The subject is a male aged 33 to 37. Dermoscopy of a skin lesion.
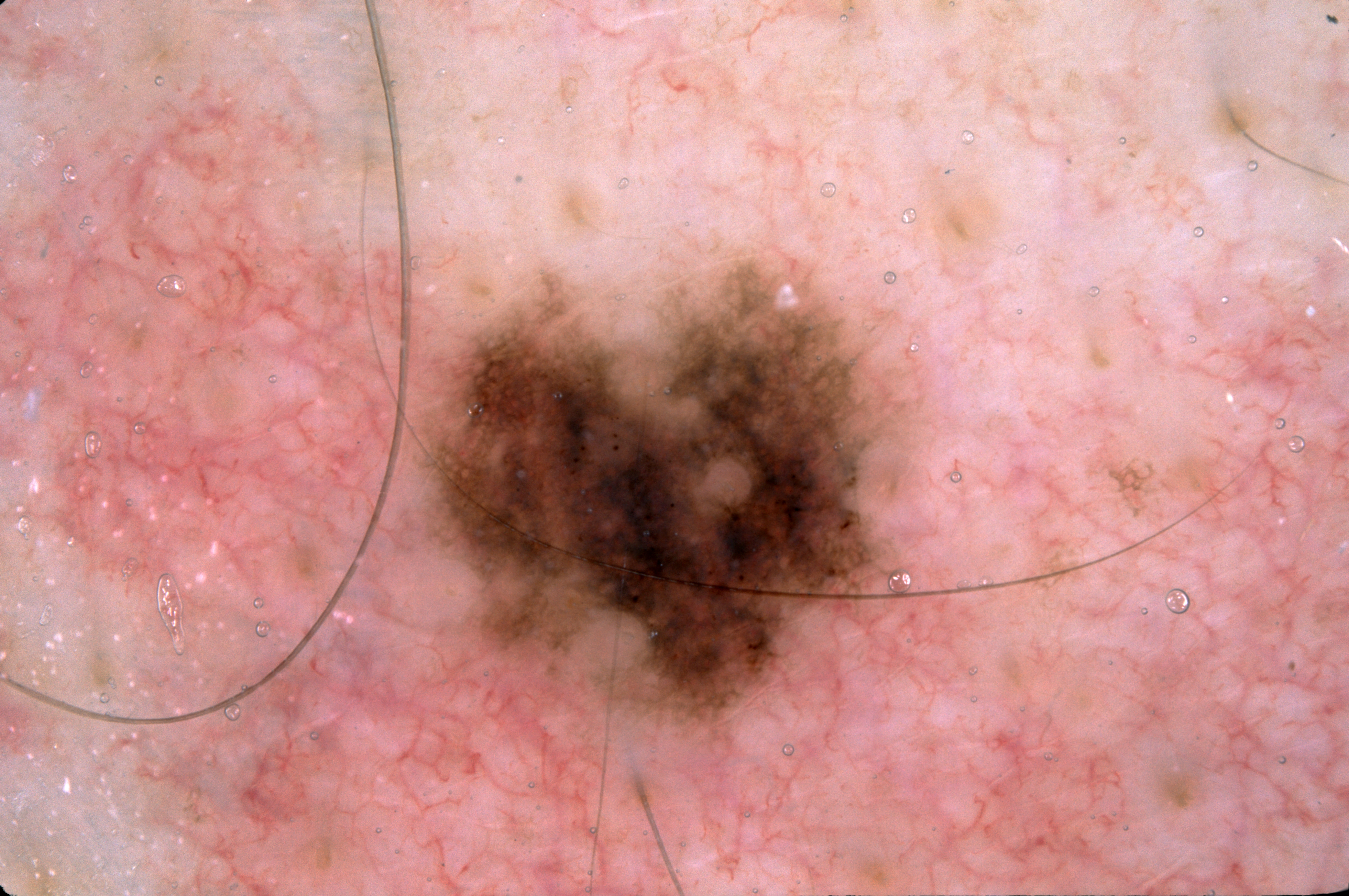Dermoscopic examination shows pigment network, with no streaks, negative network, or milia-like cysts. A mid-sized lesion within the field. The lesion spans <box>411, 266, 907, 728</box>. The lesion was assessed as a melanocytic nevus, a benign lesion.